The affected area is the back of the torso. The photo was captured at an angle. Reported duration is about one day. FST II. Self-categorized by the patient as a rash: 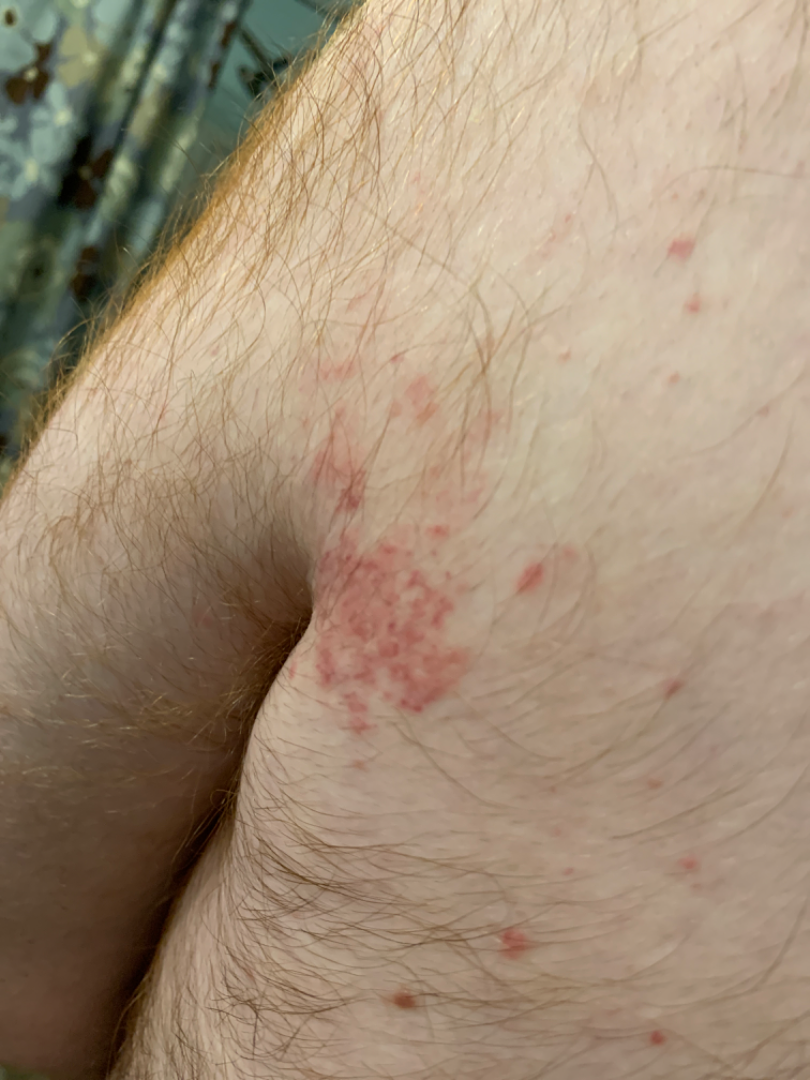{"differential": {"tied_lead": ["Eczema", "Allergic Contact Dermatitis"]}}